A dermoscopic image of a skin lesion.
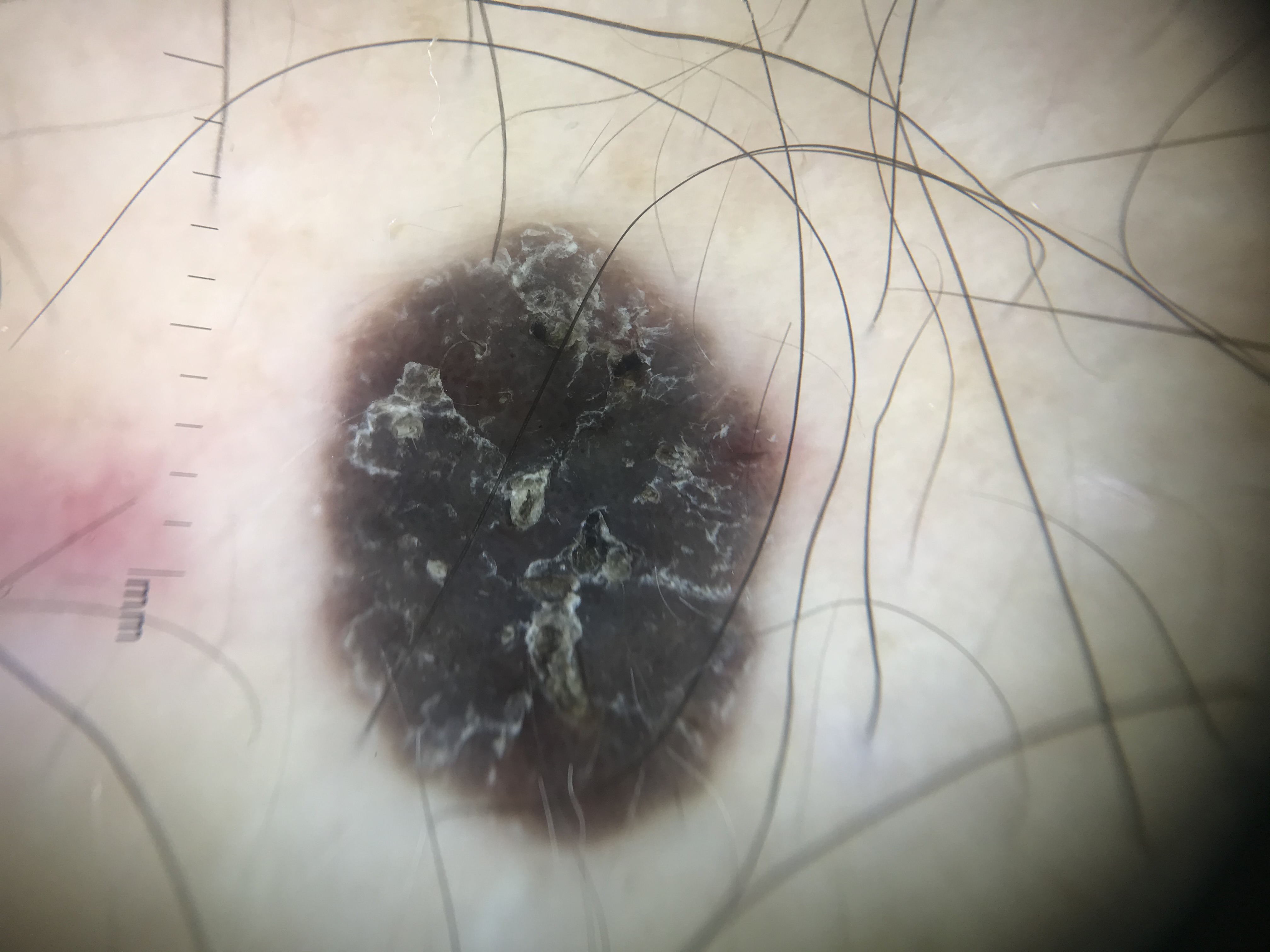The morphology is that of a keratinocytic lesion.
The diagnosis was a seborrheic keratosis.